A skin lesion imaged with a dermatoscope: 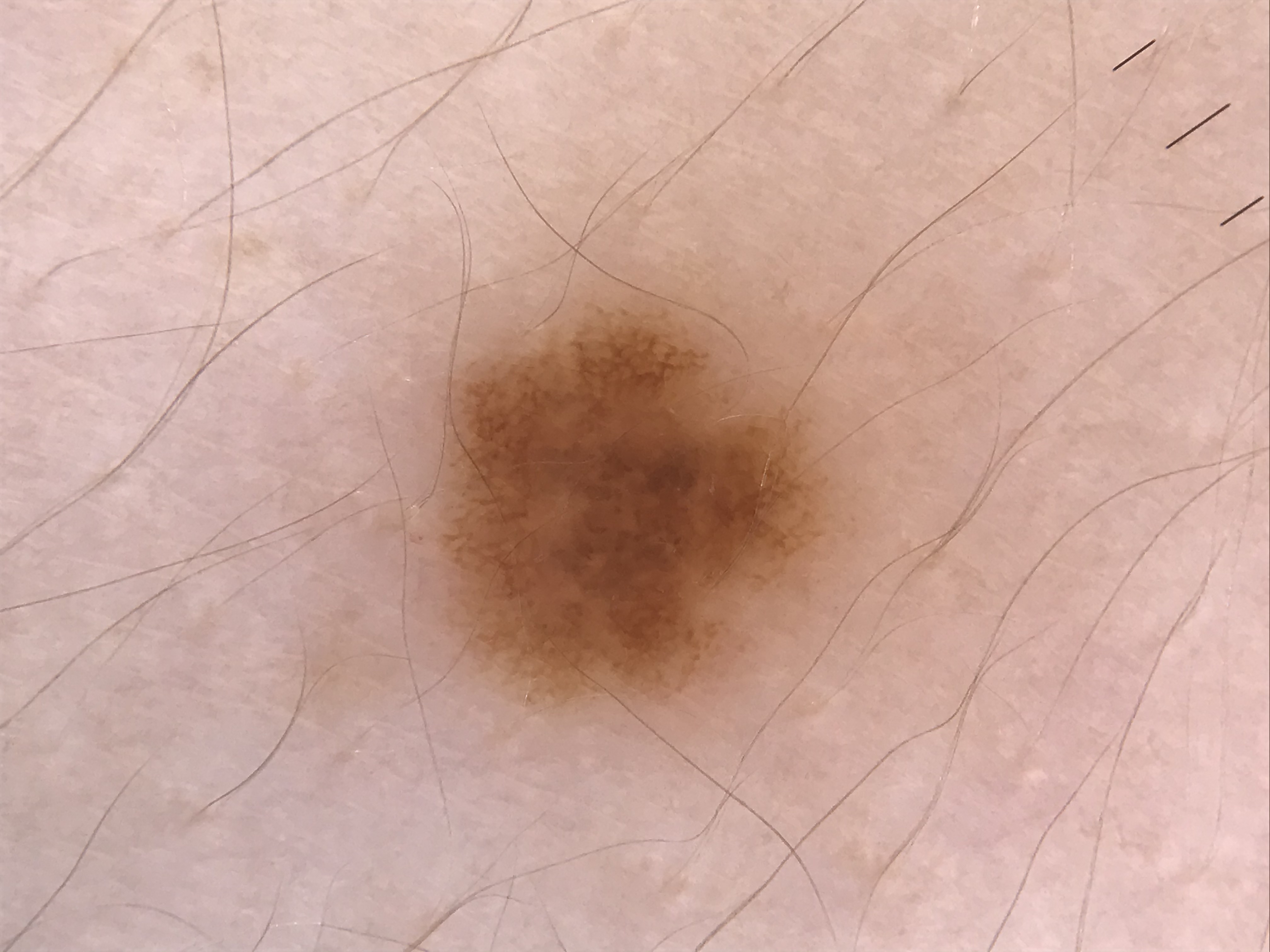Labeled as a benign lesion — a dysplastic junctional nevus.